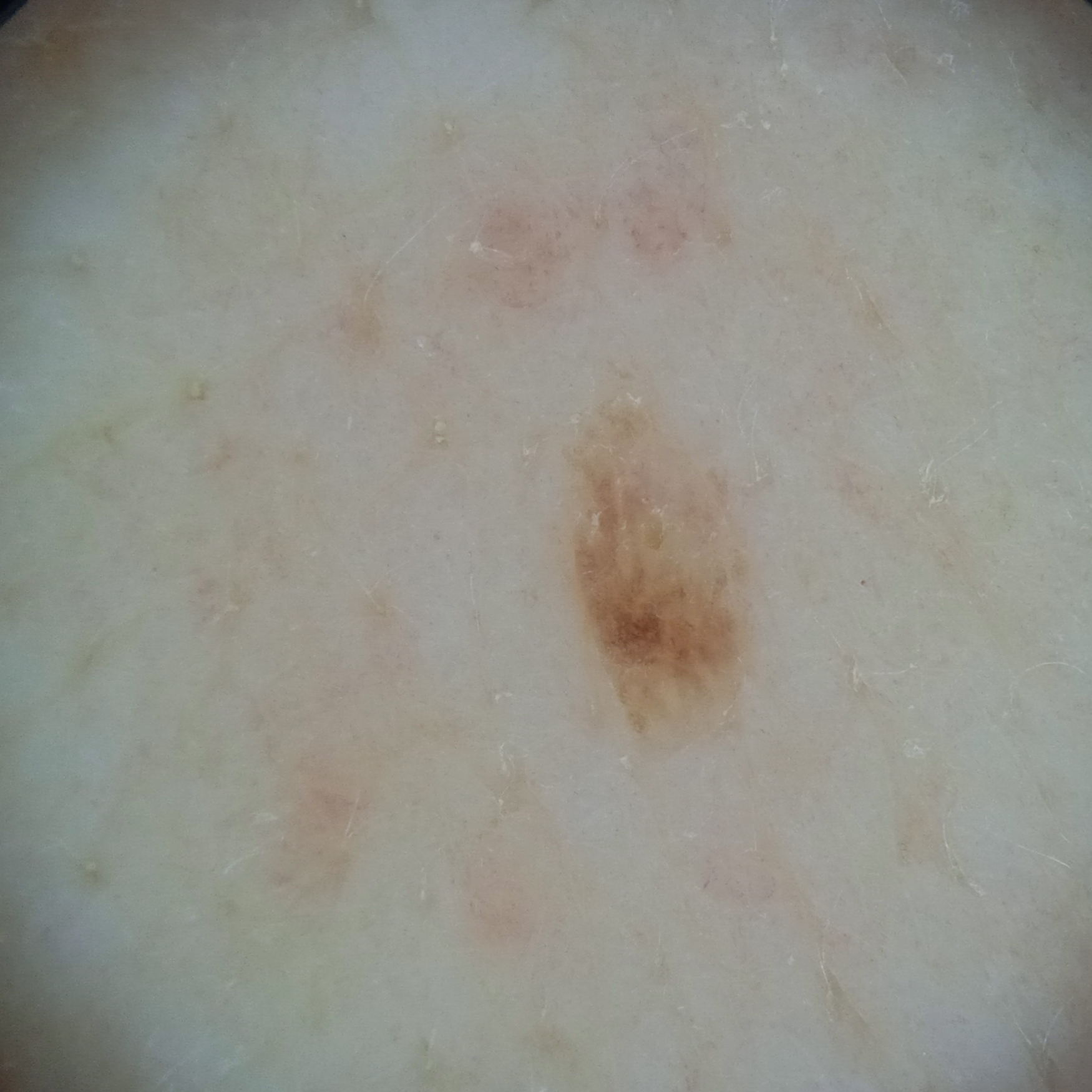Case summary:
By self-report, a personal history of skin cancer, a personal history of cancer, and no family history of skin cancer. A female patient aged 71. The patient says their skin reddens with sun exposure. Imaged for a research study, with no referral diagnosis recorded. A skin lesion imaged with a dermatoscope. Few moles overall by the patient's own estimate. The lesion is located on the back. Measuring roughly 3.8 mm.
Impression:
The consensus diagnosis for this lesion was a seborrheic keratosis.